Lay reviewers estimated a MST of 2. This image was taken at a distance: 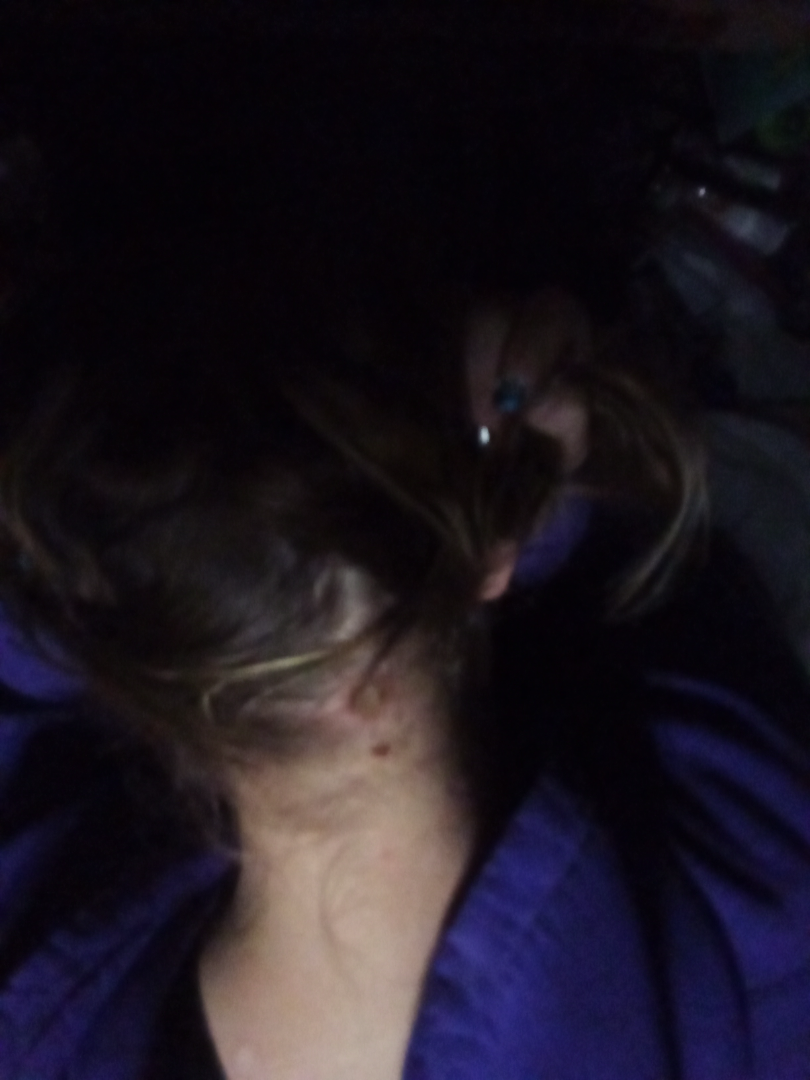The reviewing dermatologist was unable to assign a differential diagnosis from the image.